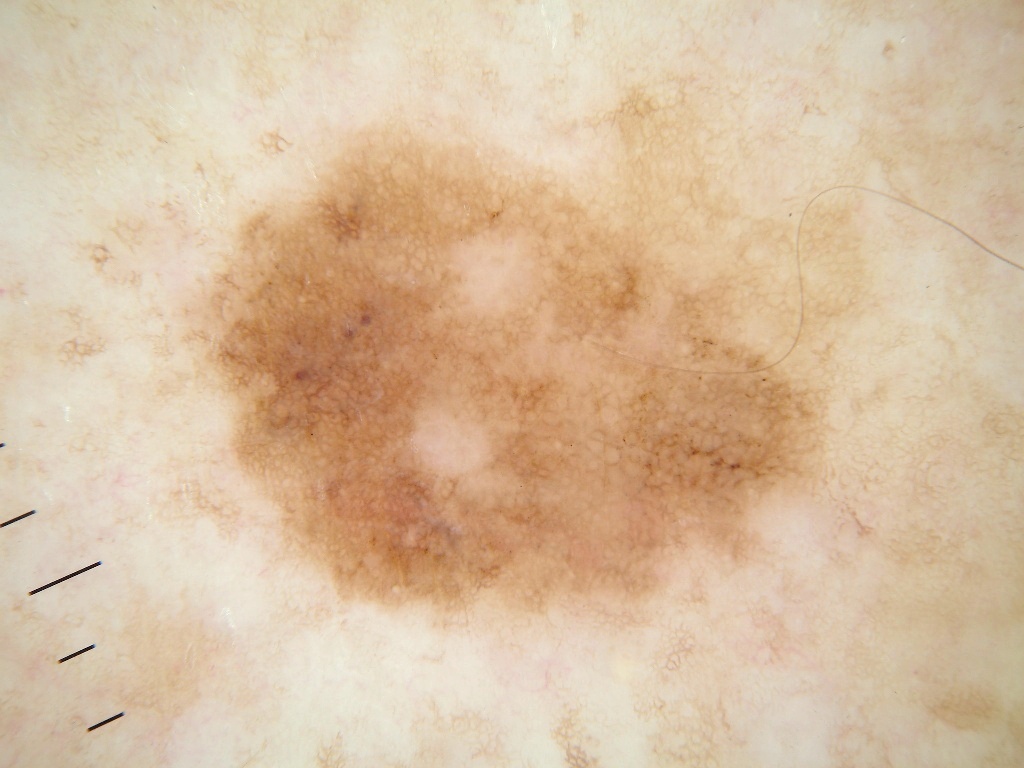This is a dermoscopic photograph of a skin lesion. A male subject, about 65 years old. The lesion covers approximately 40% of the dermoscopic field. With coordinates (x1, y1, x2, y2), the lesion occupies the region <box>178, 65, 872, 644</box>. The dermoscopic pattern shows pigment network. Histopathology confirmed a melanoma, a skin cancer.